A male patient aged 38 to 42 · a dermoscopic close-up of a skin lesion — 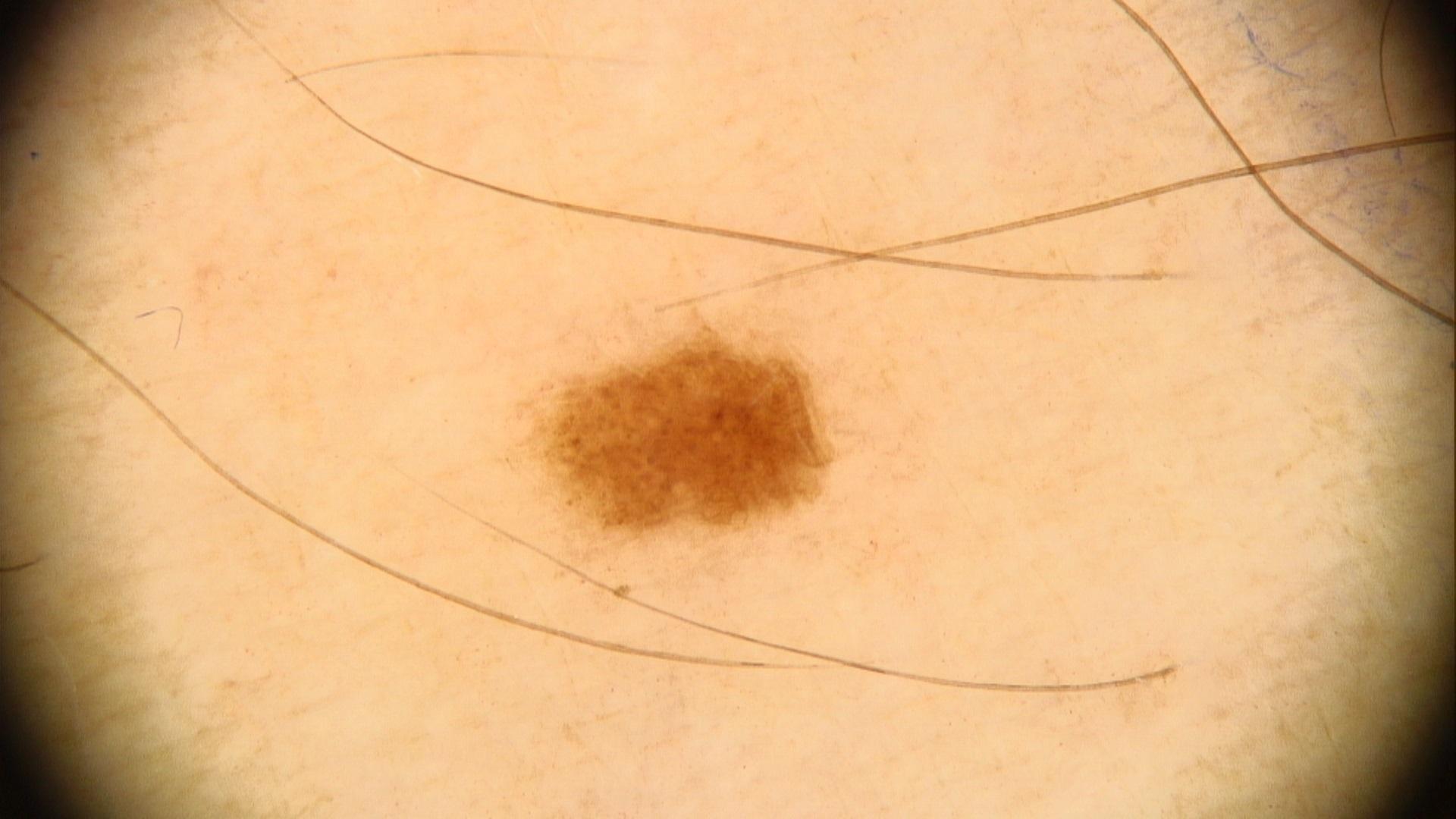Q: Where on the body is the lesion?
A: a lower extremity
Q: What is this lesion?
A: Nevus